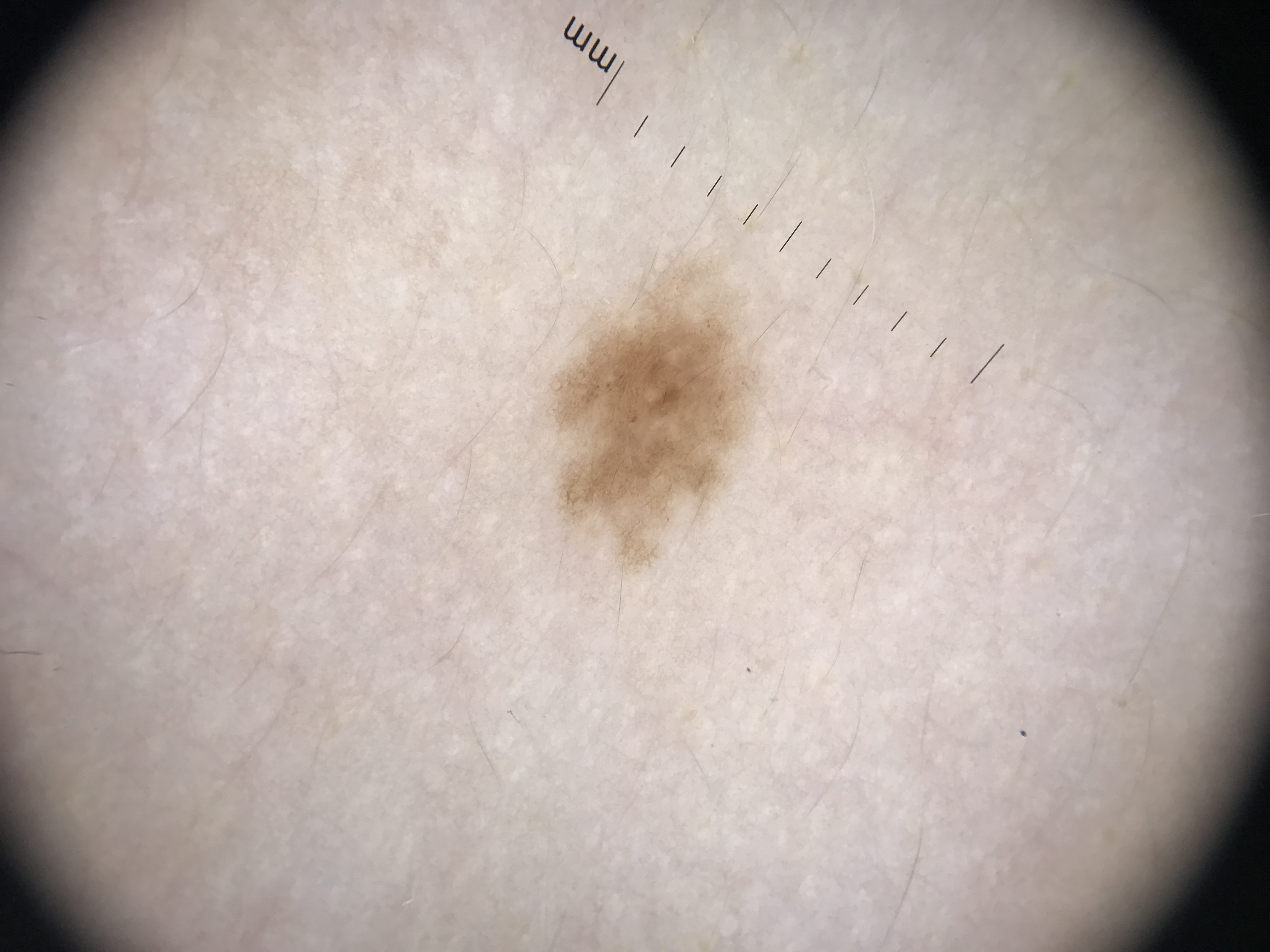imaging = dermoscopy, label = dysplastic junctional nevus (expert consensus).